The affected area is the front of the torso. This is a close-up image: 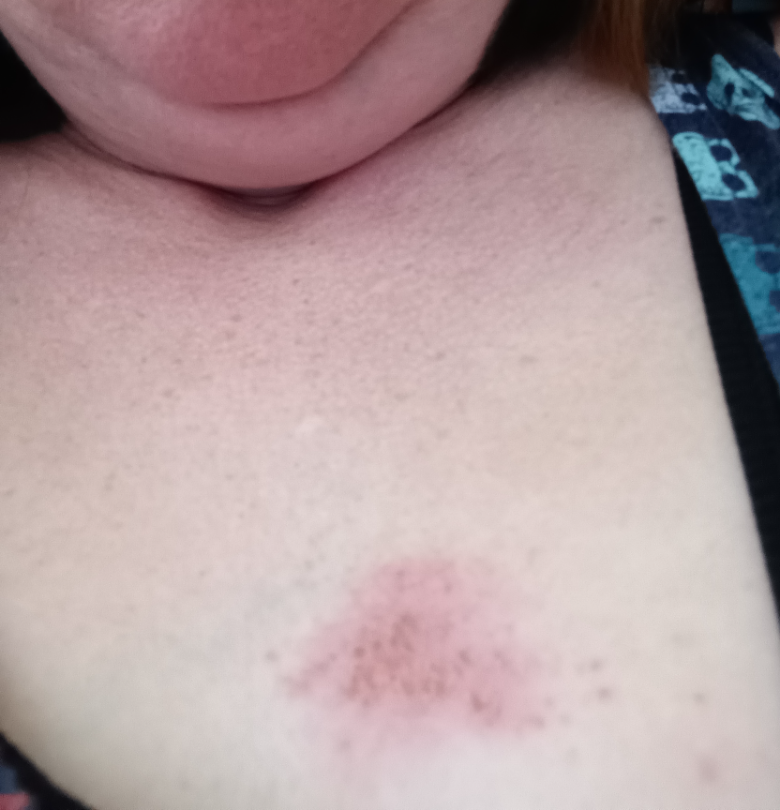assessment=ungradable on photographic review
other reported symptoms=none reported
described texture=rough or flaky
symptom duration=less than one week
patient describes the issue as=a rash